A skin lesion imaged with a dermatoscope.
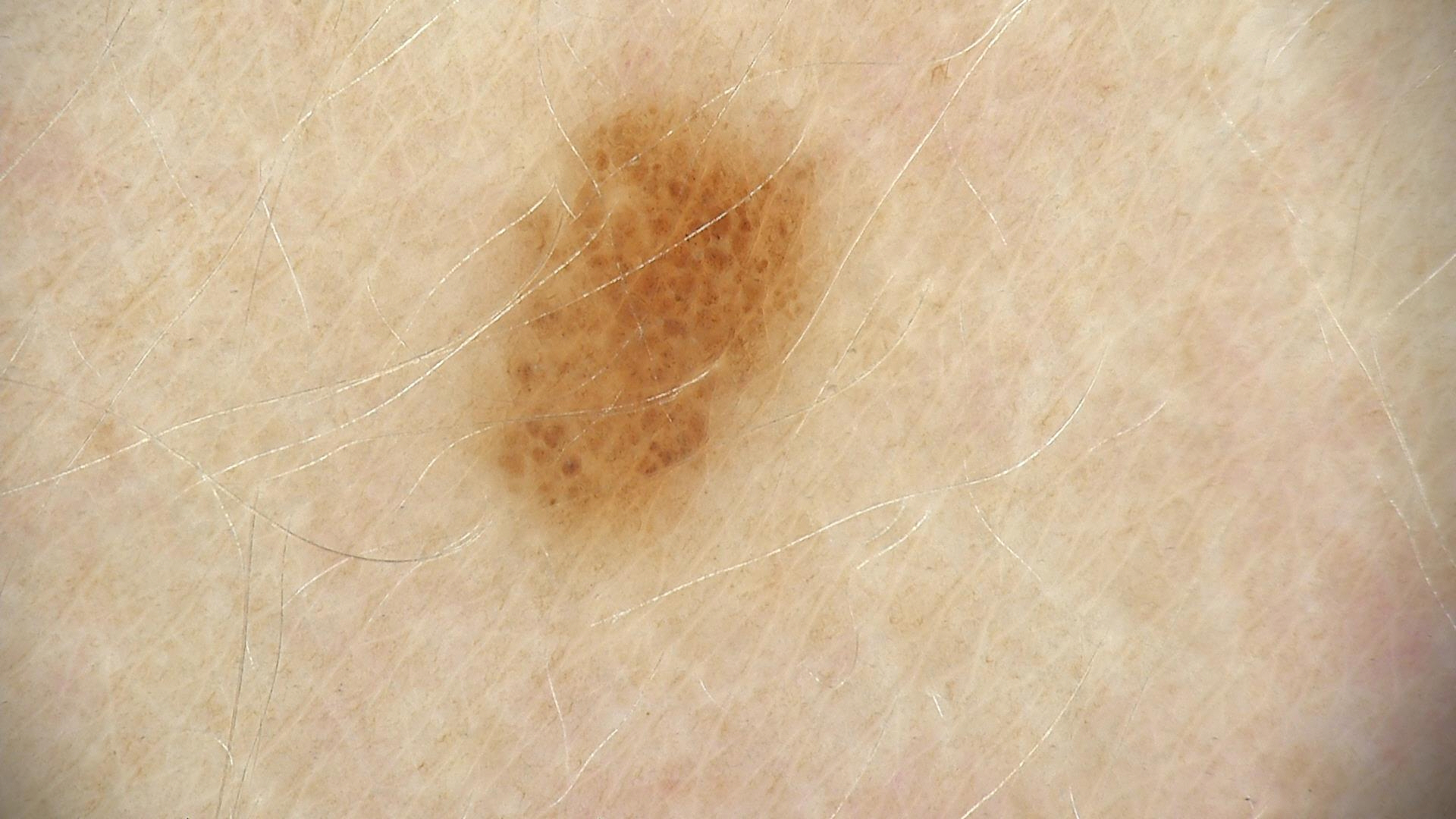The diagnosis was a banal lesion — a junctional nevus.